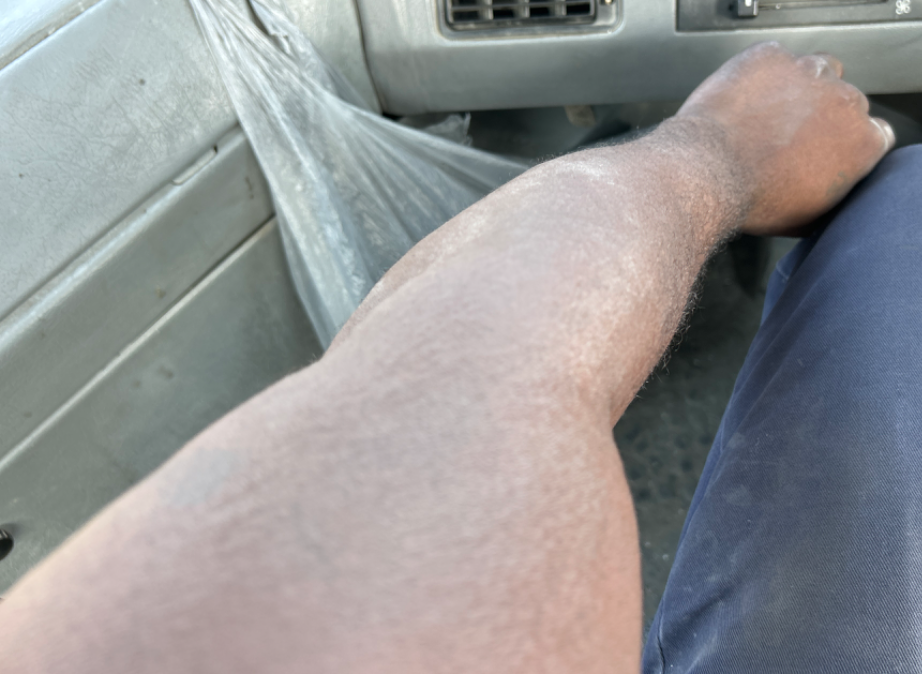- duration: less than one week
- image framing: at an angle
- reported symptoms: itching
- anatomic site: arm
- lesion texture: flat
- clinical impression: most consistent with Eczema